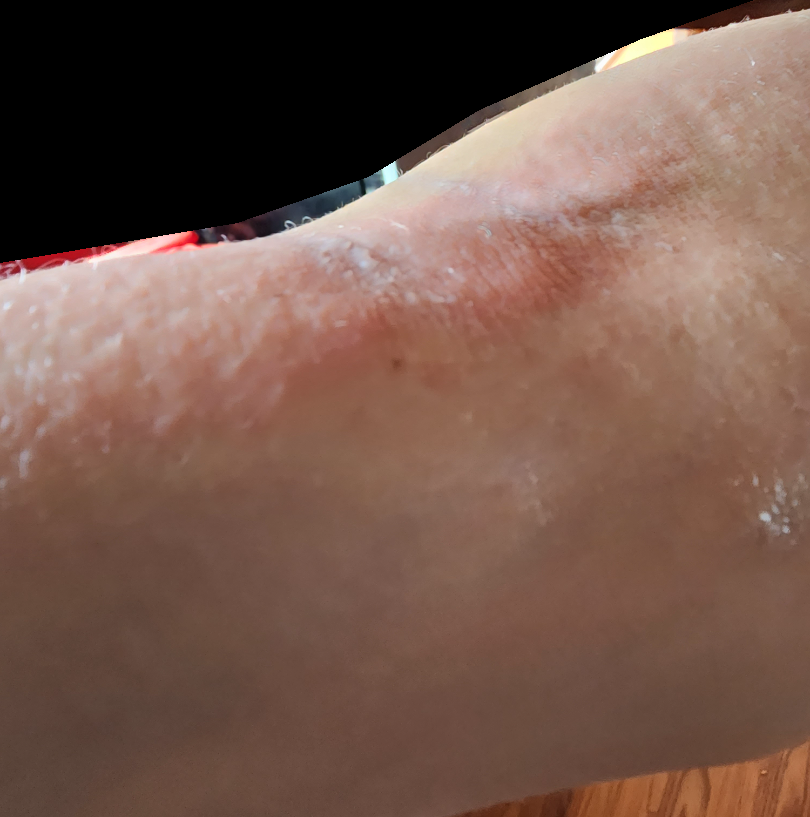Diagnostic features were not clearly distinguishable in this photograph. The contributor notes the condition has been present for less than one week. The patient described the issue as a rash. The affected area is the arm. The photo was captured at an angle. Texture is reported as raised or bumpy. No associated systemic symptoms reported.